The patient says their skin reddens with sun exposure. A female subject aged 26. Imaged for a research study, with no referral diagnosis recorded. A clinical photograph of a skin lesion:
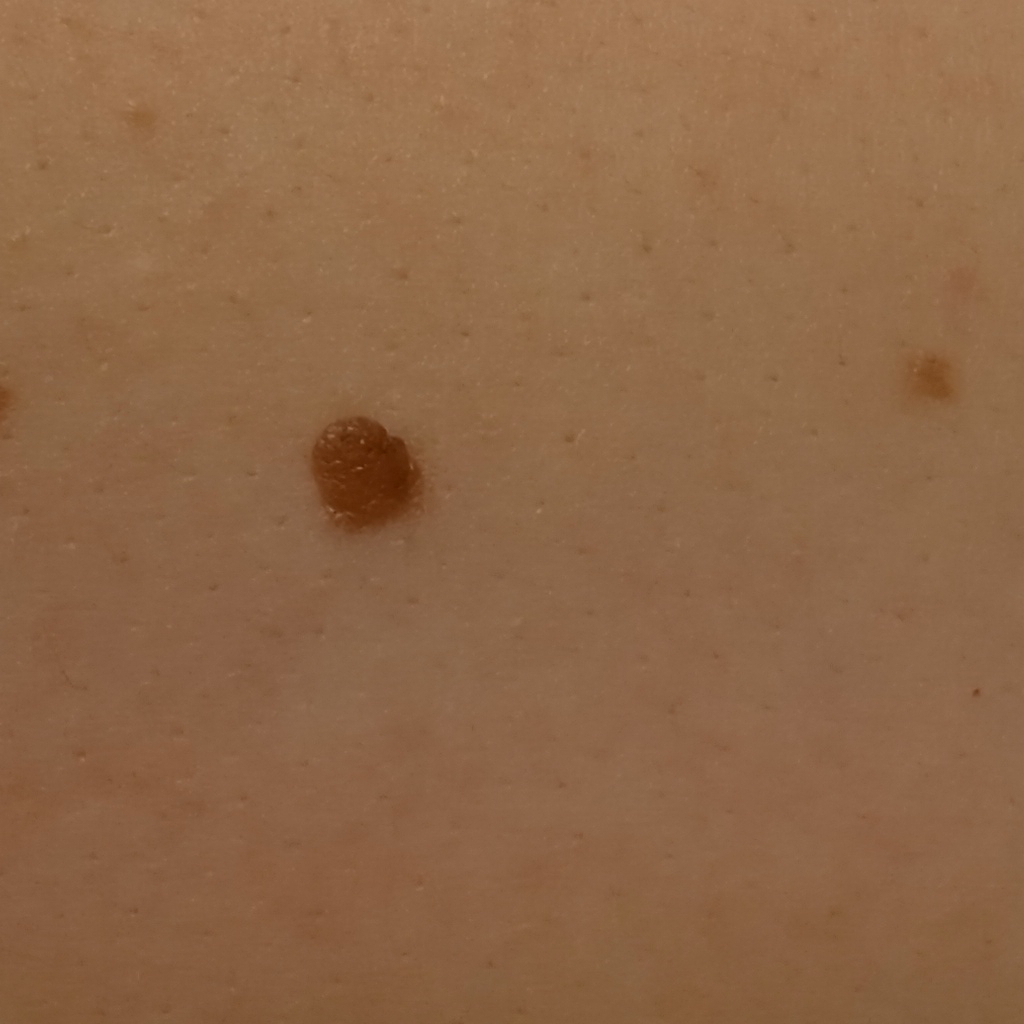location = the back
lesion size = 5.5 mm
diagnosis = melanocytic nevus (dermatologist consensus)